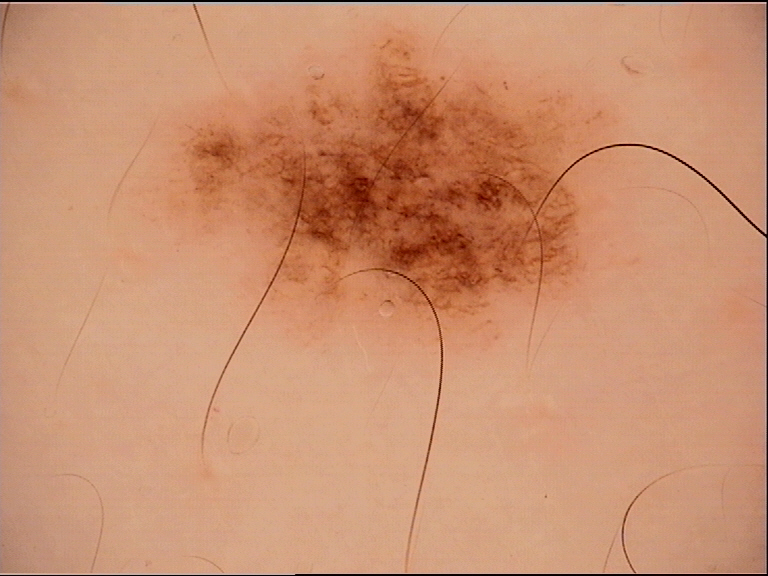modality: dermatoscopy; diagnostic label: dysplastic junctional nevus (expert consensus).